Fitzpatrick II. The photograph is a close-up of the affected area. The patient is female.
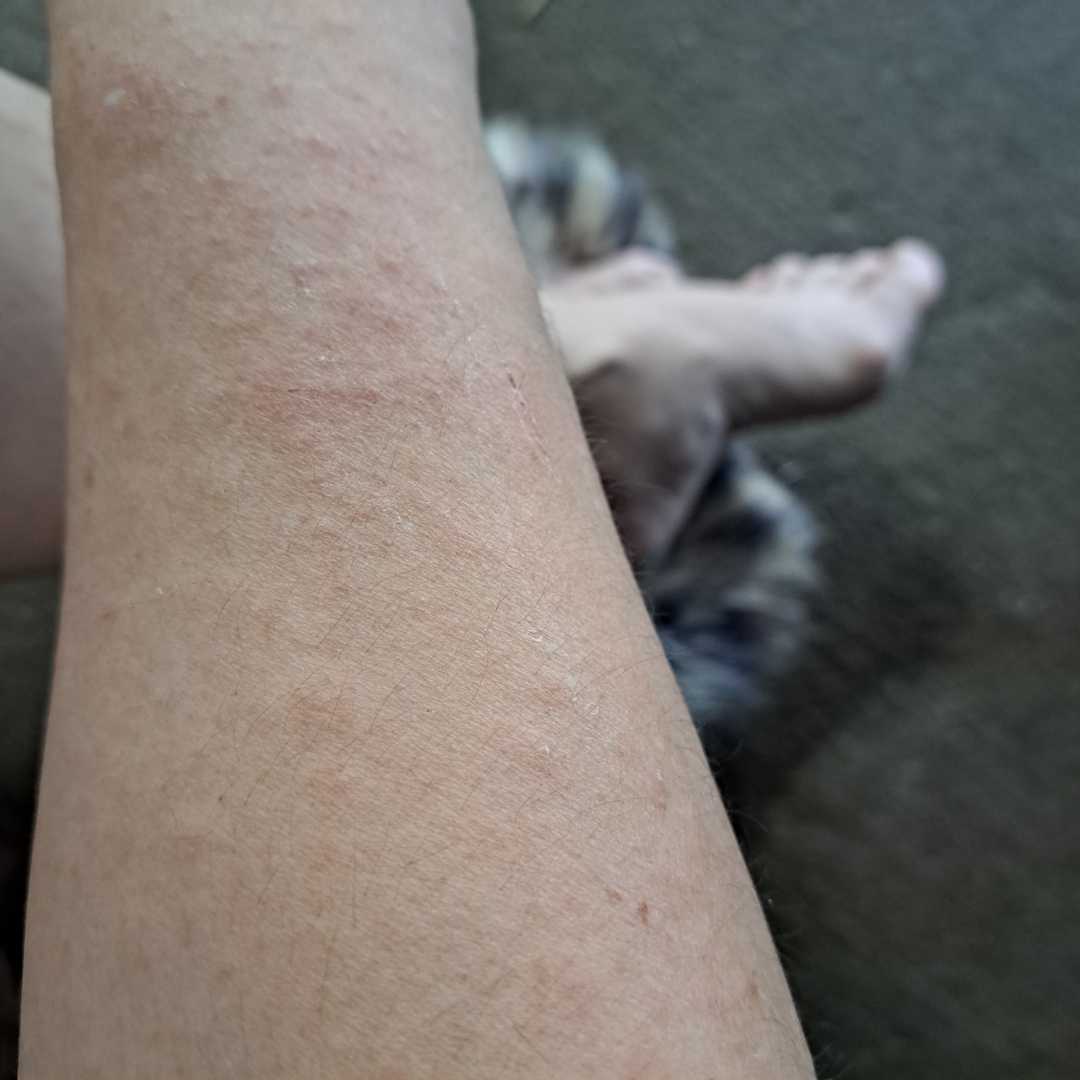impression = single-reviewer assessment: in keeping with Eczema